A contact-polarized dermoscopy image of a skin lesion. A female subject in their mid- to late 30s.
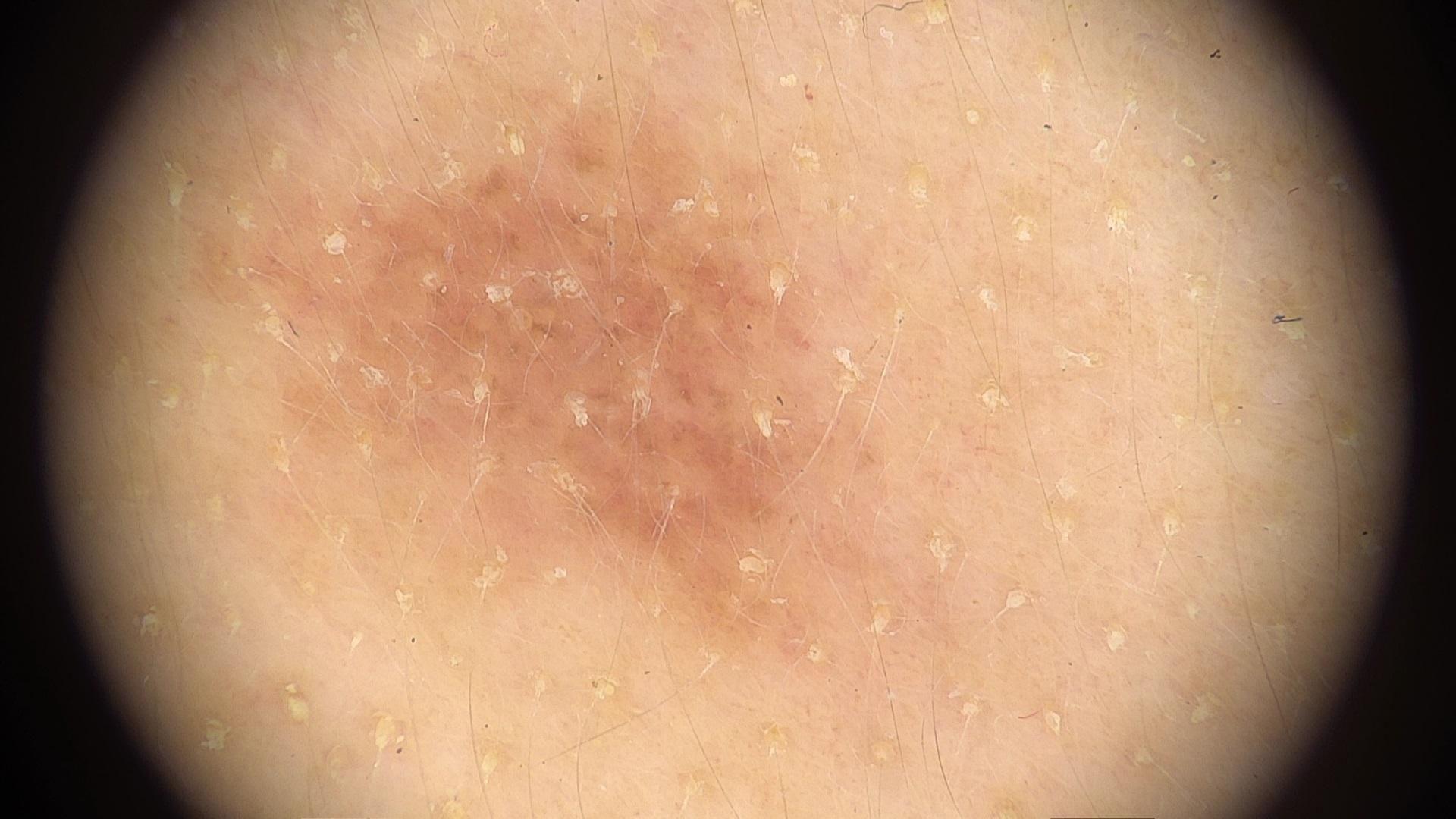Located on the head or neck.
The diagnostic impression was a nevus.